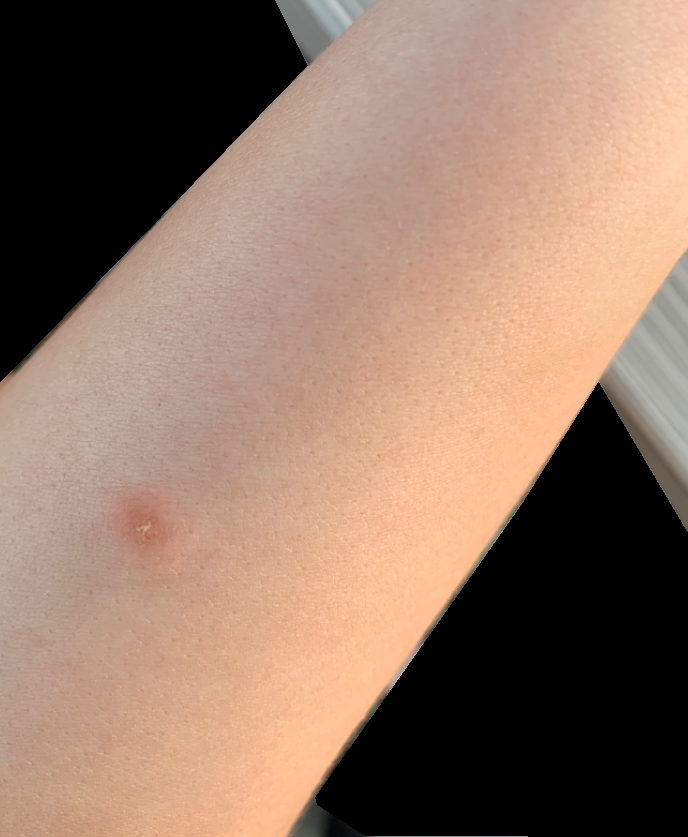Impression: The case was indeterminate on photographic review.